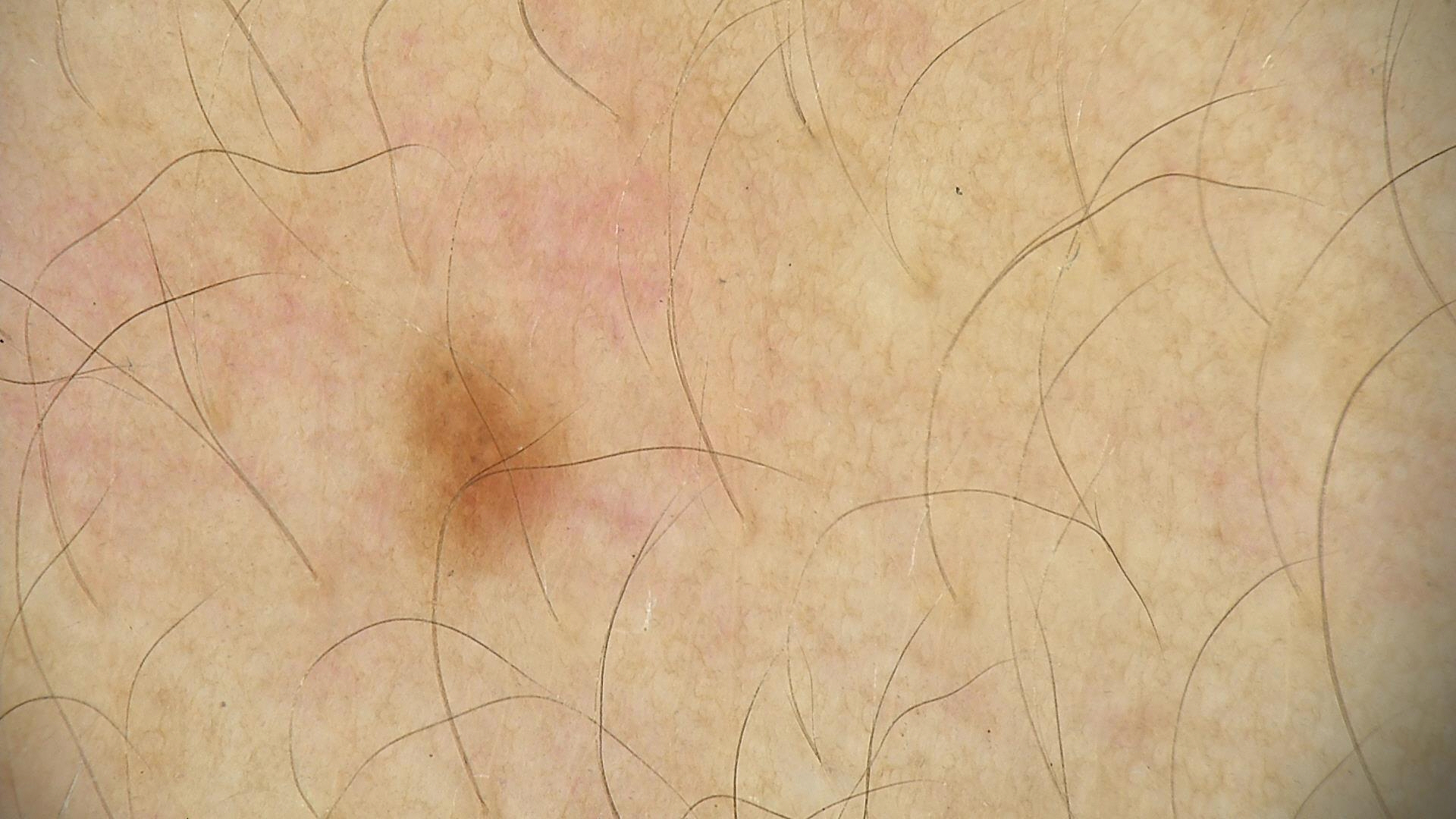class: dysplastic junctional nevus (expert consensus).